A dermoscopic view of a skin lesion — 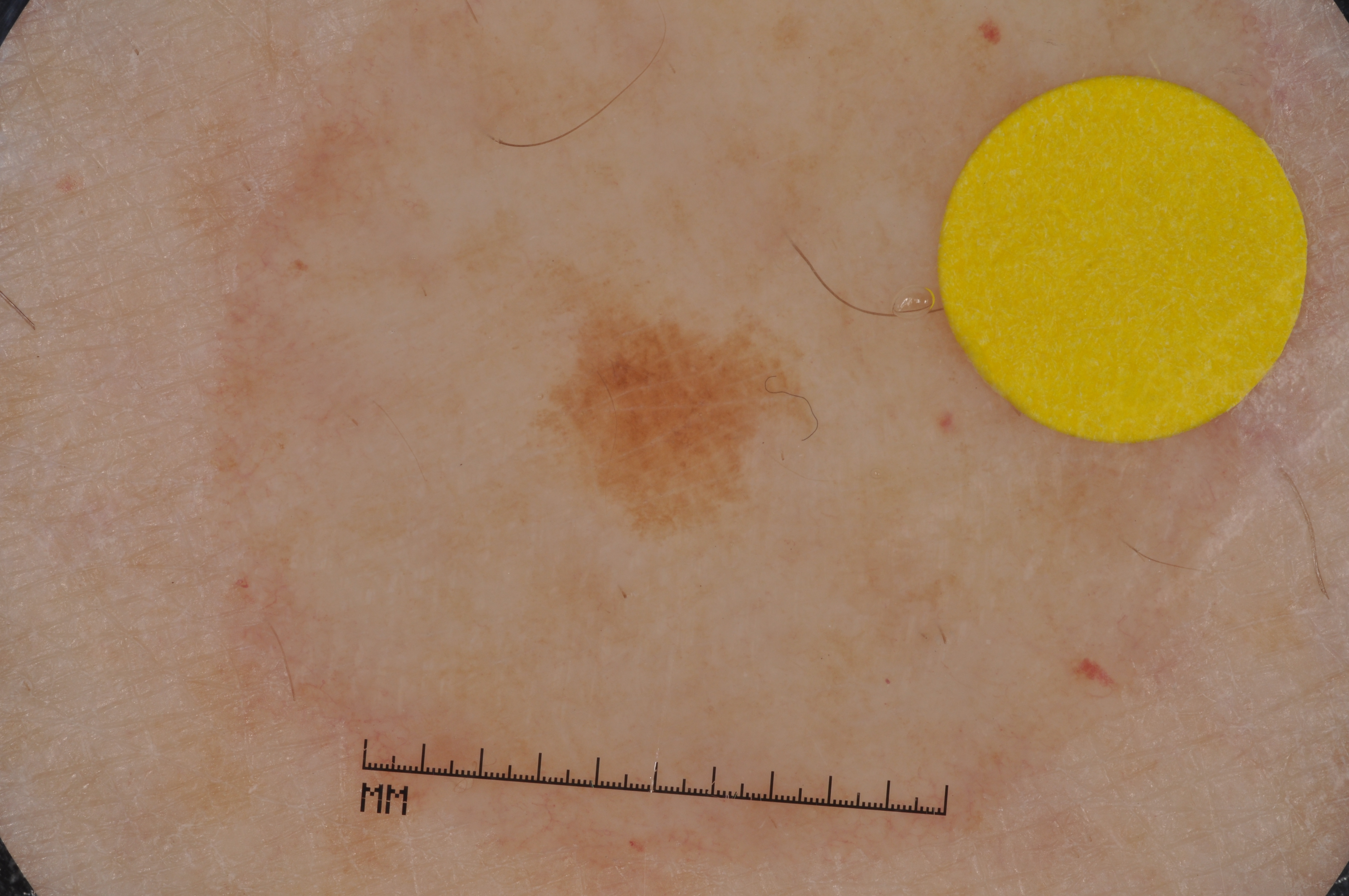With coordinates (x1, y1, x2, y2), lesion location: (559, 301, 790, 525). Clinically diagnosed as a seborrheic keratosis.